The contributor is female · close-up view · present for about one day · located on the leg.
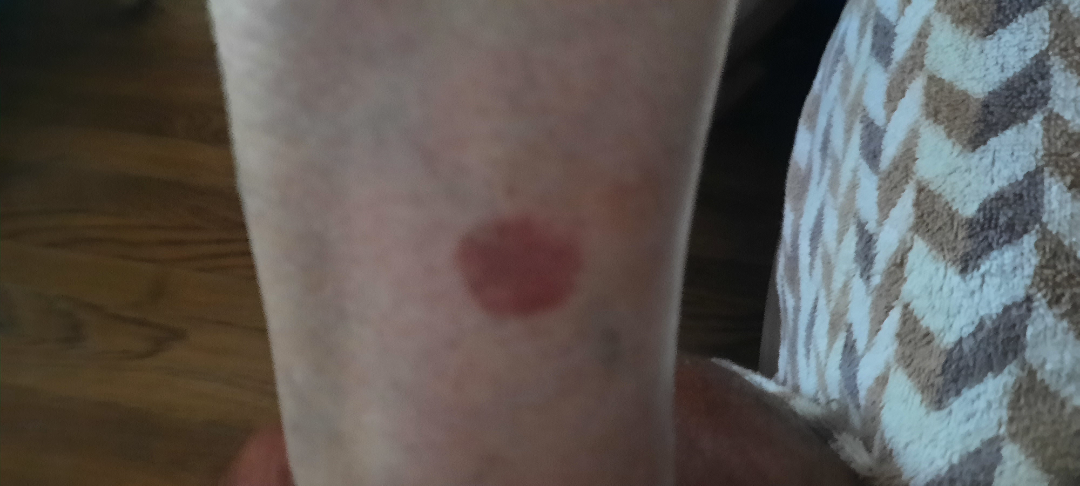The case was indeterminate on photographic review.